The lesion involves the front of the torso and arm, the photo was captured at an angle: 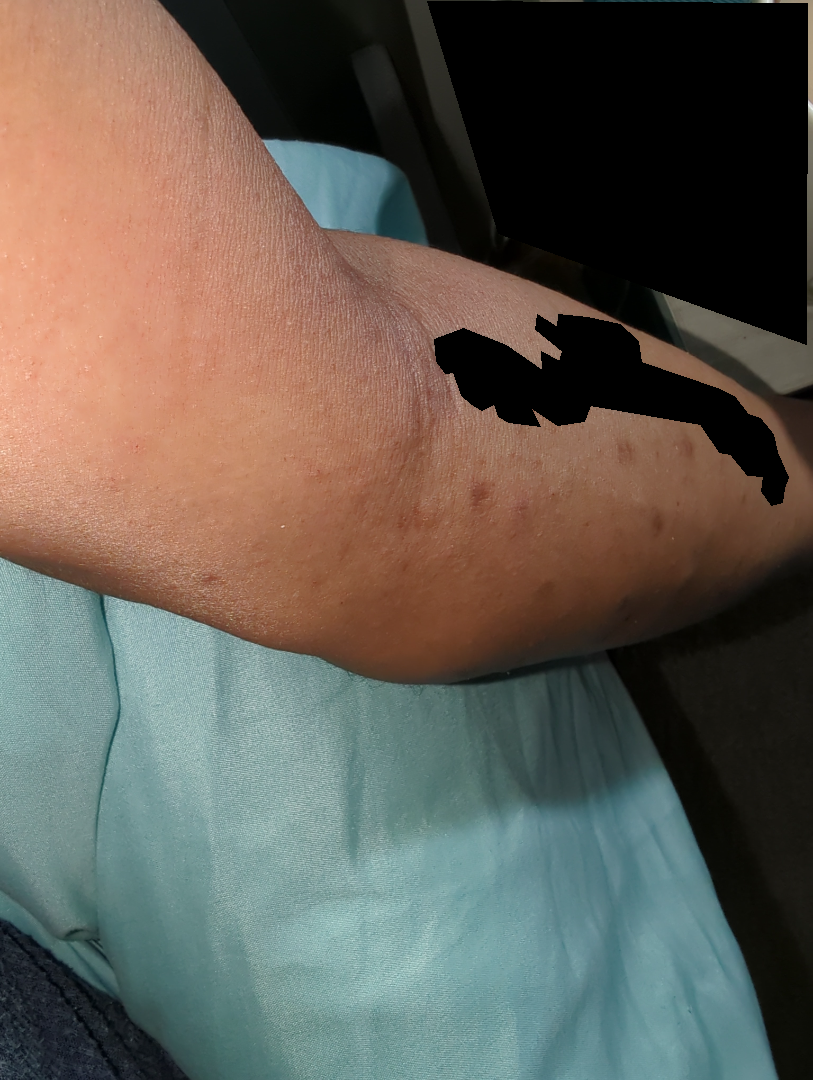The patient notes the condition has been present for one to four weeks. Symptoms reported: itching and darkening. The patient notes associated chills. The lesion is described as rough or flaky. Self-categorized by the patient as a rash. The reviewing dermatologist's impression was: in keeping with Eczema.